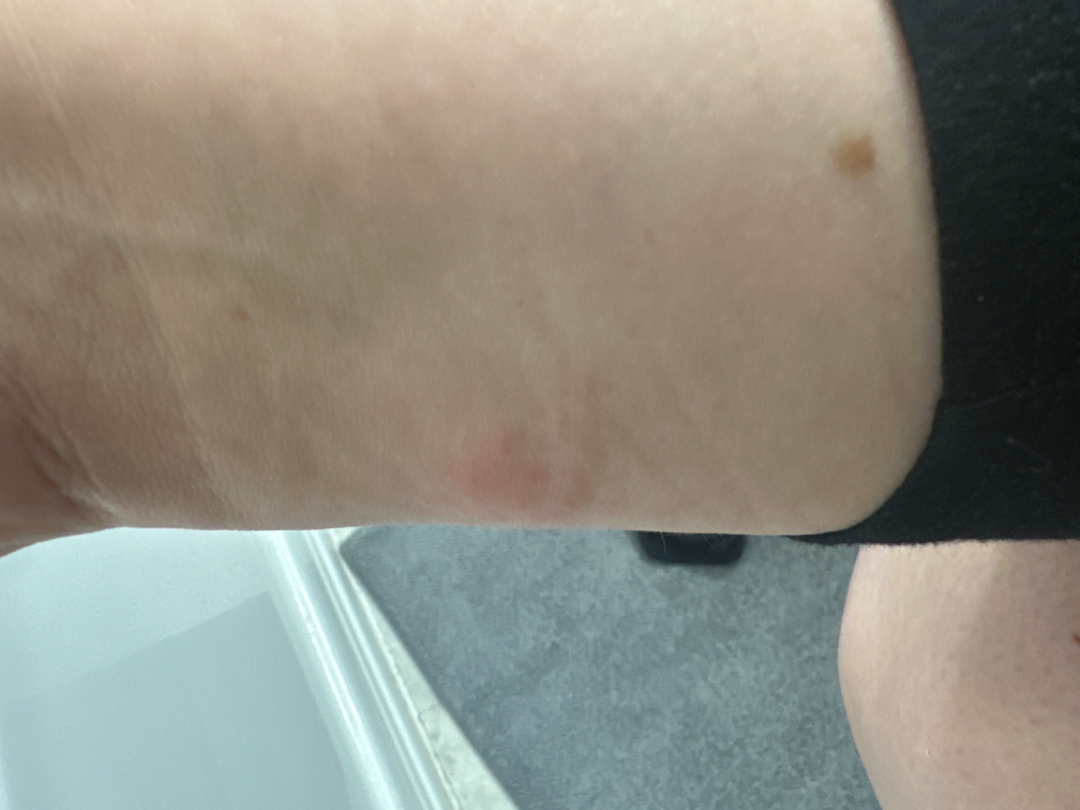An image taken at an angle.
The affected area is the arm.
One reviewing dermatologist: most likely Insect Bite; also on the differential is Allergic Contact Dermatitis; an alternative is Herpes Simplex.